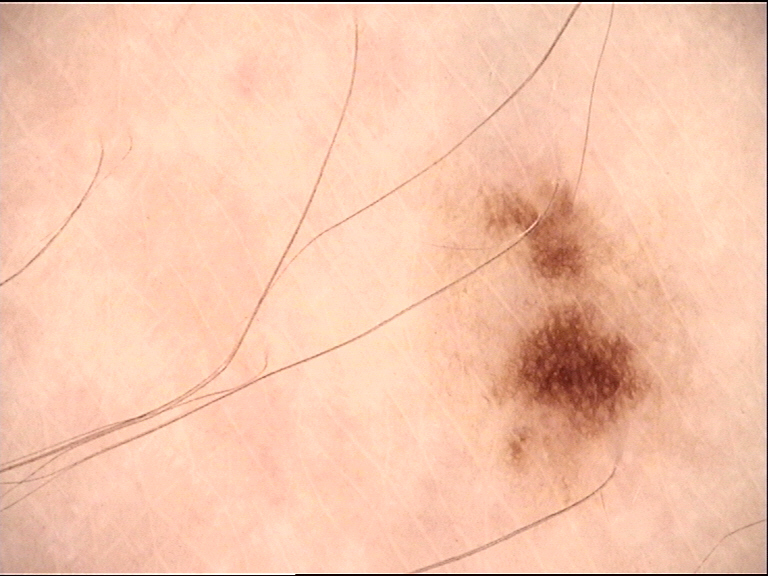label = dysplastic junctional nevus (expert consensus).